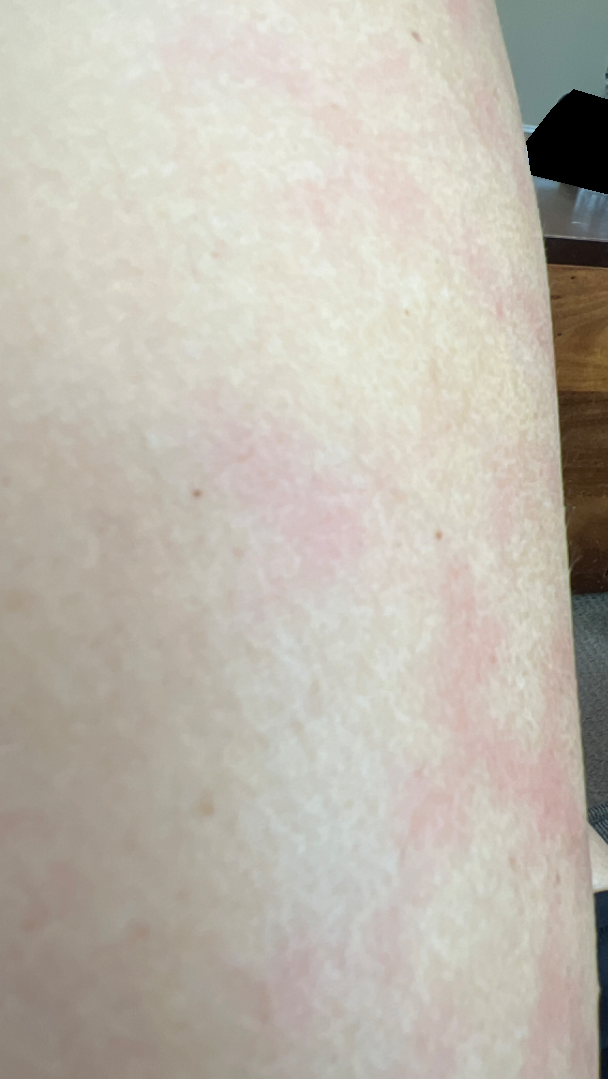– shot type · at an angle
– patient's own categorization · skin that appeared healthy to them
– site · leg
– patient · female, age 30–39
– reported symptoms · none reported
– onset · about one day
– lesion texture · flat
– differential · reviewed remotely by one dermatologist: most consistent with Livedo reticularis; an alternative is Erythema ab igne